A dermatoscopic image of a skin lesion.
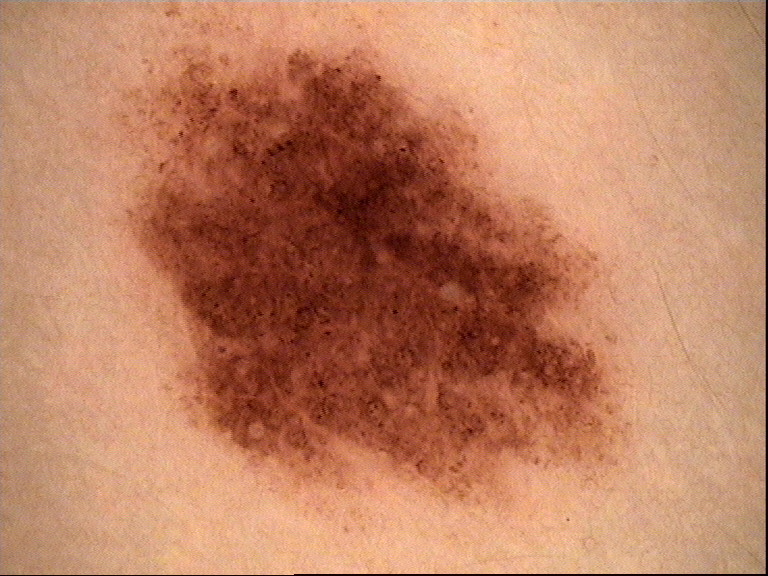<dermoscopy>
<diagnosis>
<name>dysplastic junctional nevus</name>
<code>jd</code>
<malignancy>benign</malignancy>
<super_class>melanocytic</super_class>
<confirmation>expert consensus</confirmation>
</diagnosis>
</dermoscopy>